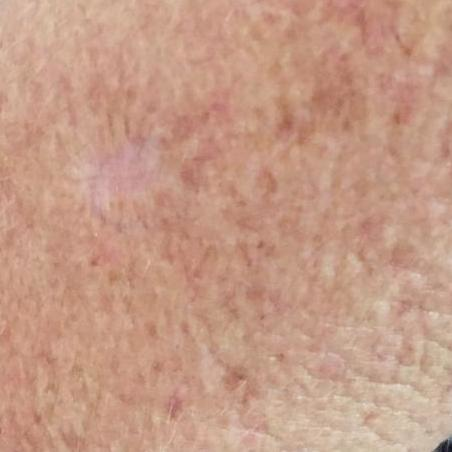A clinical photo of a skin lesion taken with a smartphone. A subject aged 65. The lesion was found on an arm. The patient describes that the lesion itches, but has not bled and does not hurt. Consistent with a lesion with uncertain malignant potential — an actinic keratosis.